Close-up view; located on the arm: 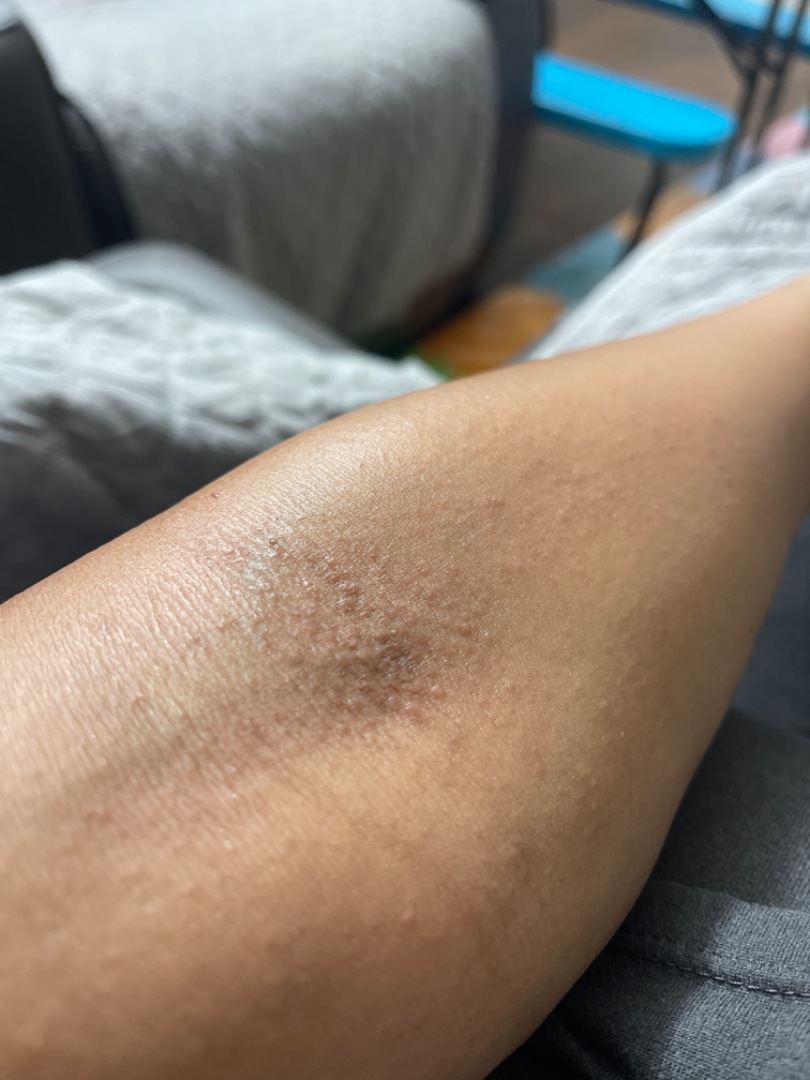Case summary:
– present for — less than one week
– patient-reported symptoms — itching and burning
– lesion texture — raised or bumpy
– diagnostic considerations — consistent with Eczema